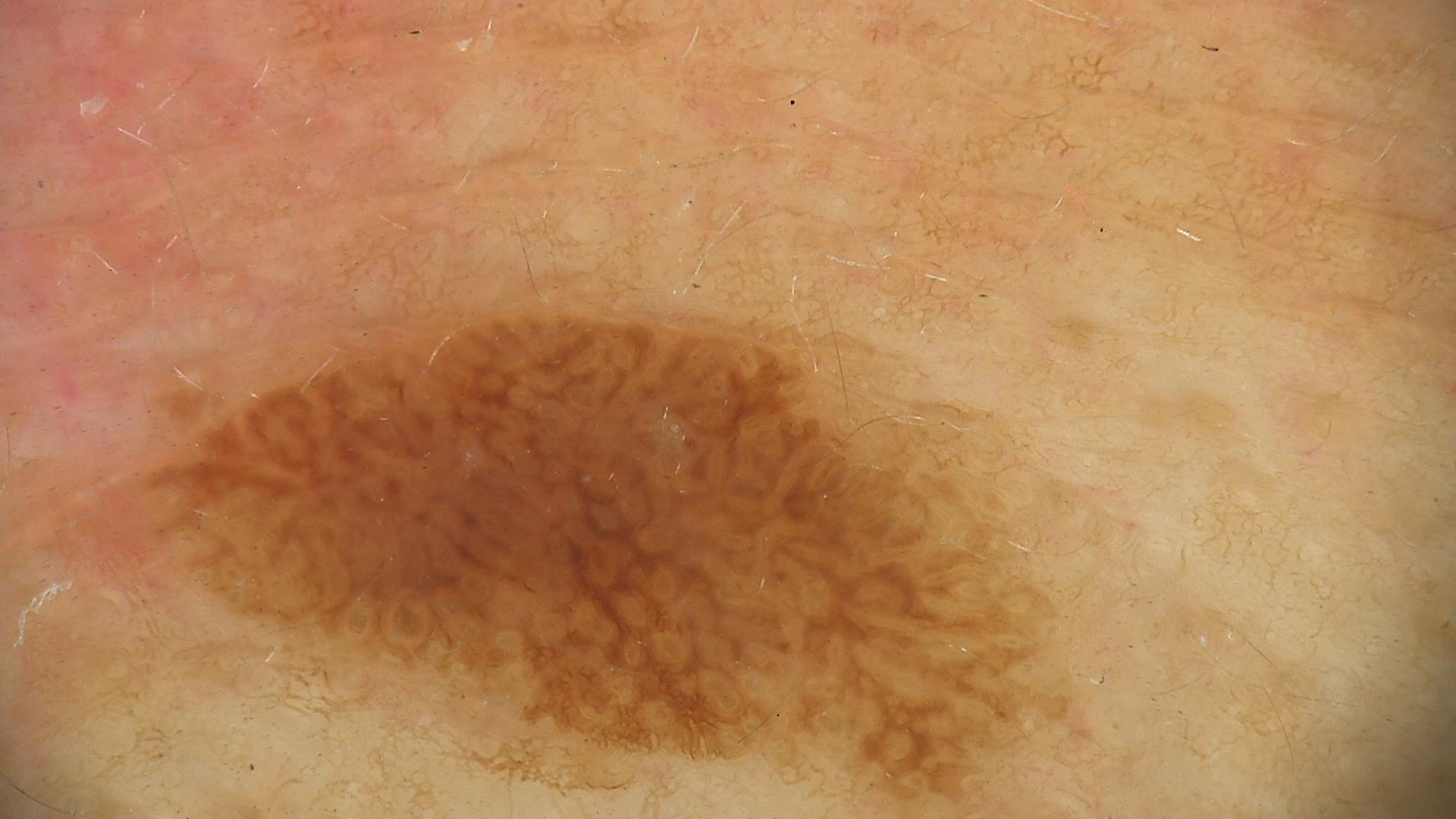Q: What is the lesion category?
A: keratinocytic
Q: What is the diagnosis?
A: seborrheic keratosis (expert consensus)